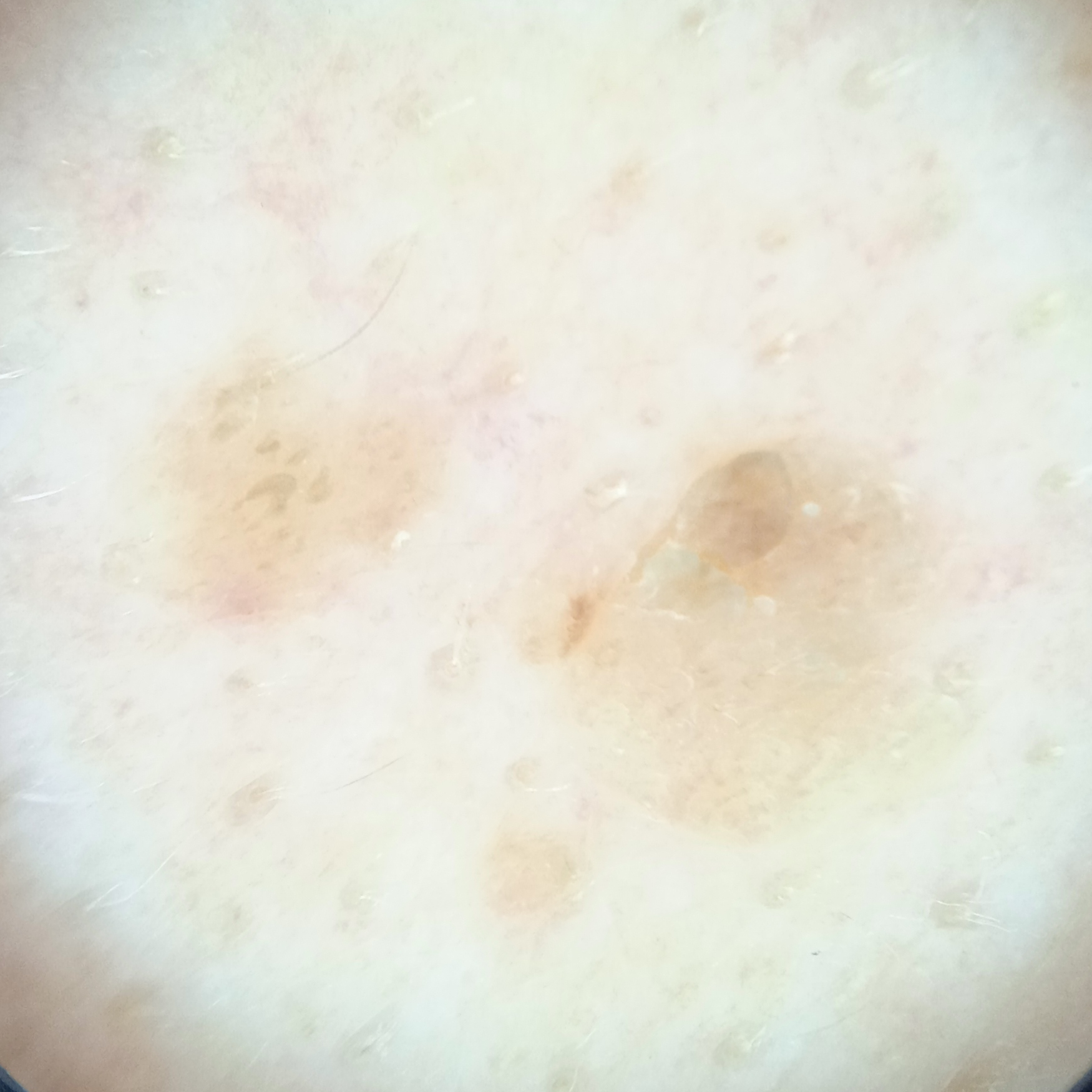nevus count = few melanocytic nevi overall
risk factors = no family history of skin cancer
assessment = seborrheic keratosis (dermatologist consensus)